A female patient age 71; a clinical close-up of a skin lesion: 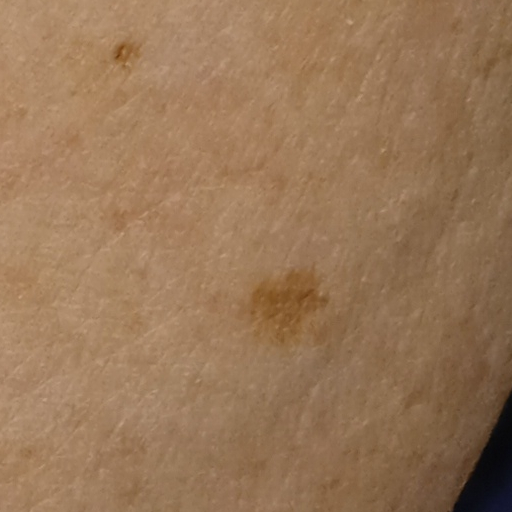Summary:
The lesion is located on an arm. Measuring roughly 6.1 mm.
Impression:
The dermatologists' assessment was a melanocytic nevus.